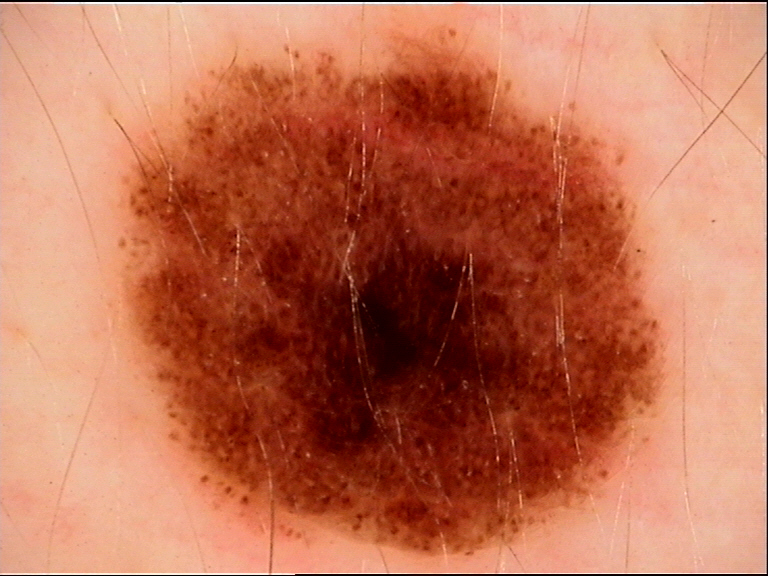Diagnosed as a dysplastic junctional nevus.